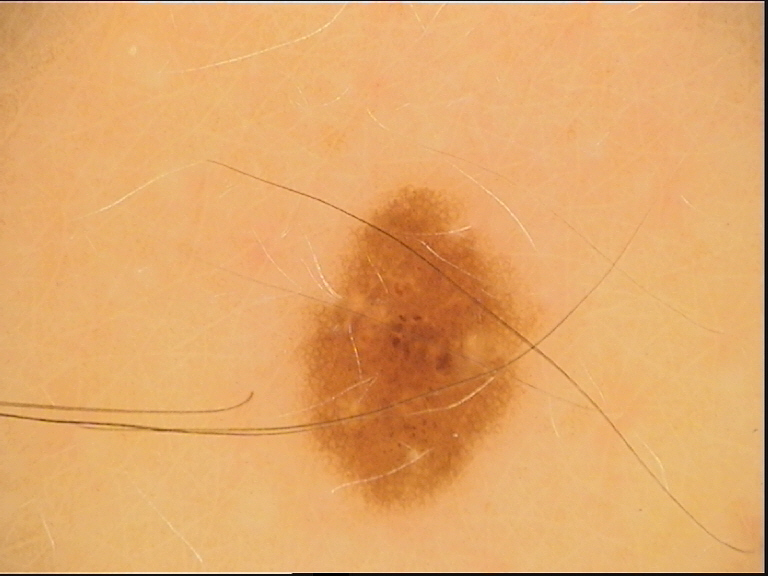The diagnosis was a dysplastic junctional nevus.